Per the chart, a first-degree relative with melanoma · the patient was assessed as Fitzpatrick phototype III · a female subject aged around 35:
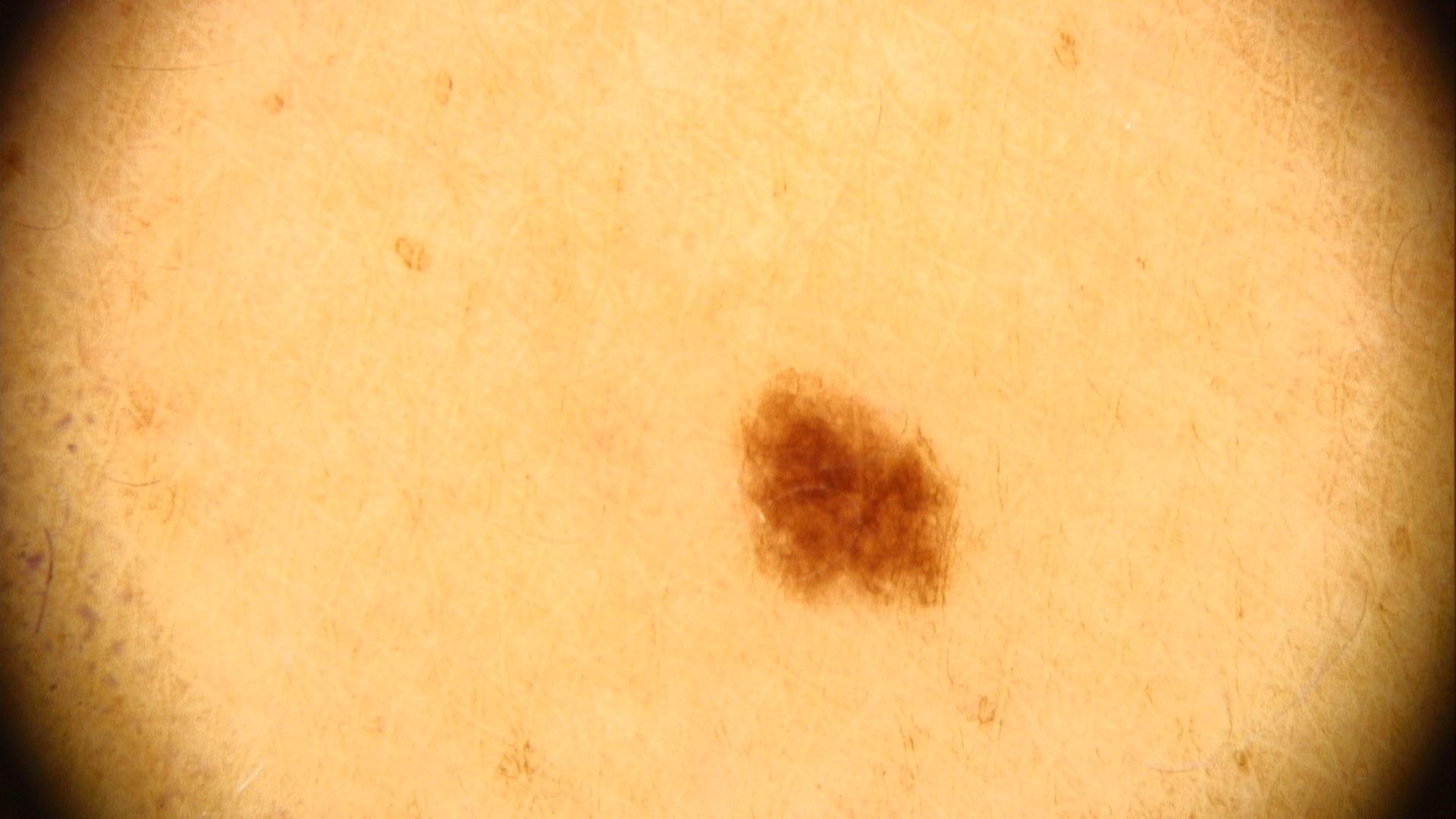Case summary: The lesion is on a lower extremity. Conclusion: The diagnostic impression was a lesion of melanocytic lineage — a nevus.